The back of the torso is involved · the contributor is a female aged 50–59 · a close-up photograph.
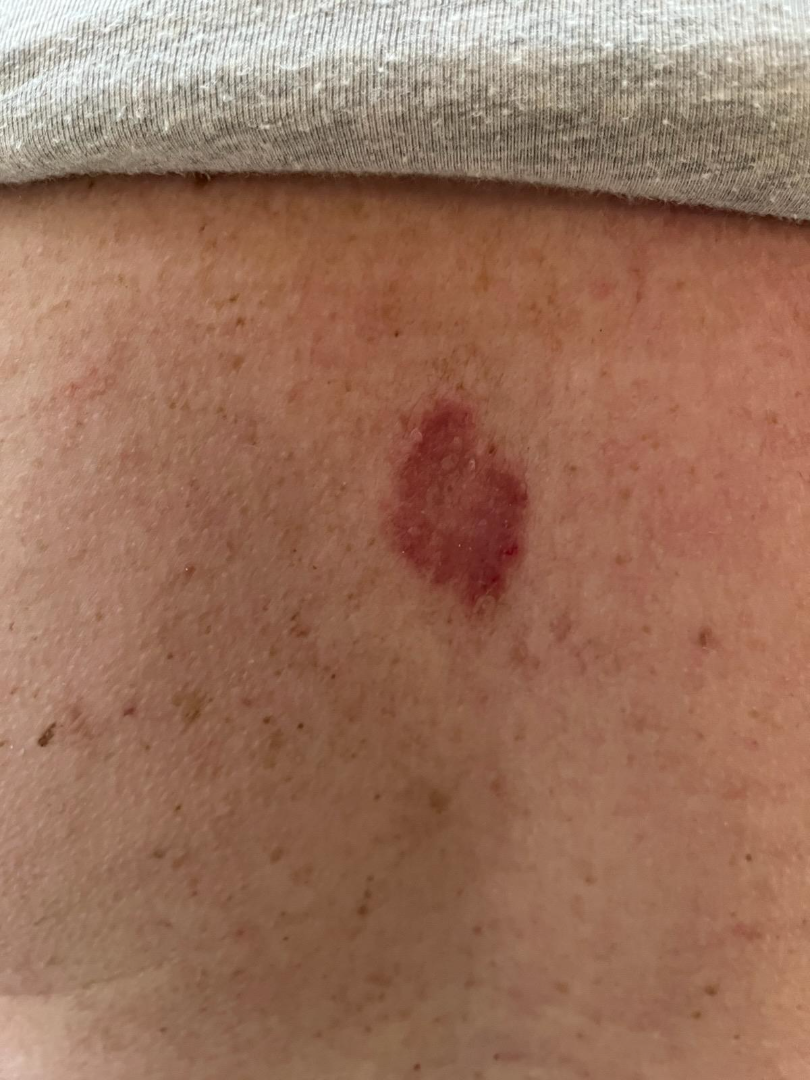Findings:
• associated systemic symptoms · none reported
• reported symptoms · bothersome appearance
• surface texture · rough or flaky
• symptom duration · less than one week
• patient's own categorization · a rash
• differential · most consistent with Basal Cell Carcinoma; also consider SCC/SCCIS; less probable is Eczema